An image taken at an angle. The affected area is the head or neck. The patient is 40–49, female:
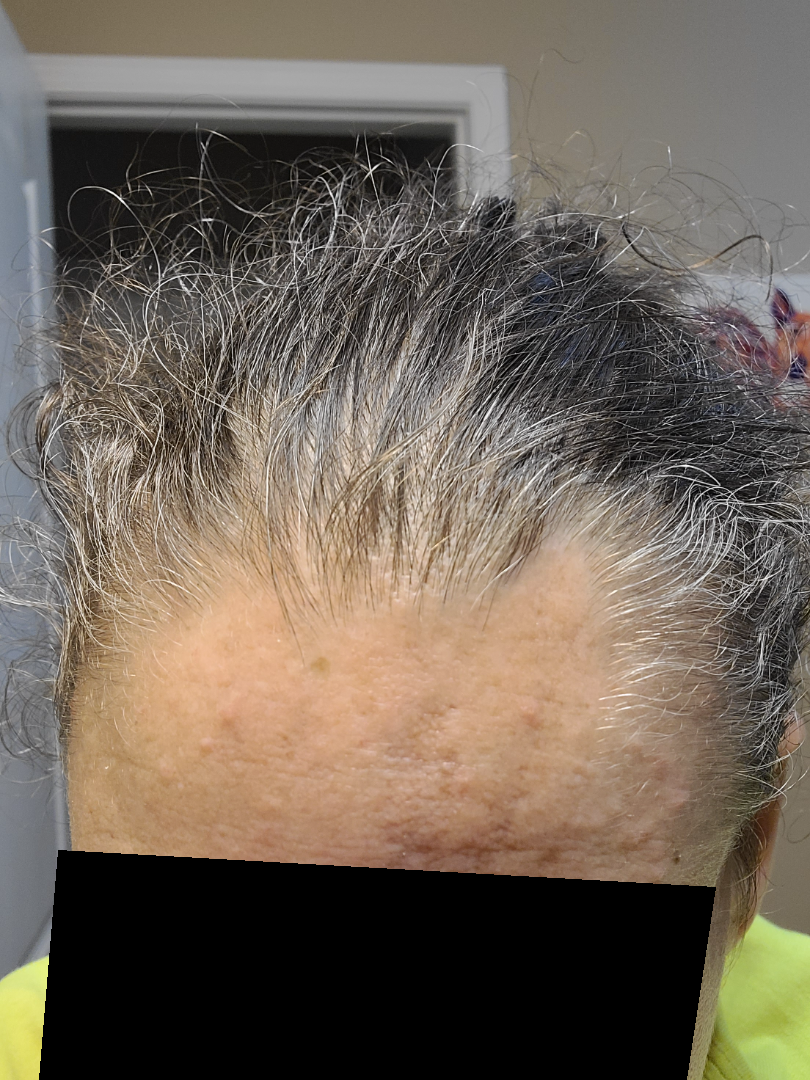Assessment:
The skin findings could not be characterized from the image.
Clinical context:
The lesion is described as raised or bumpy. Reported duration is about one day. Associated systemic symptoms include mouth sores.